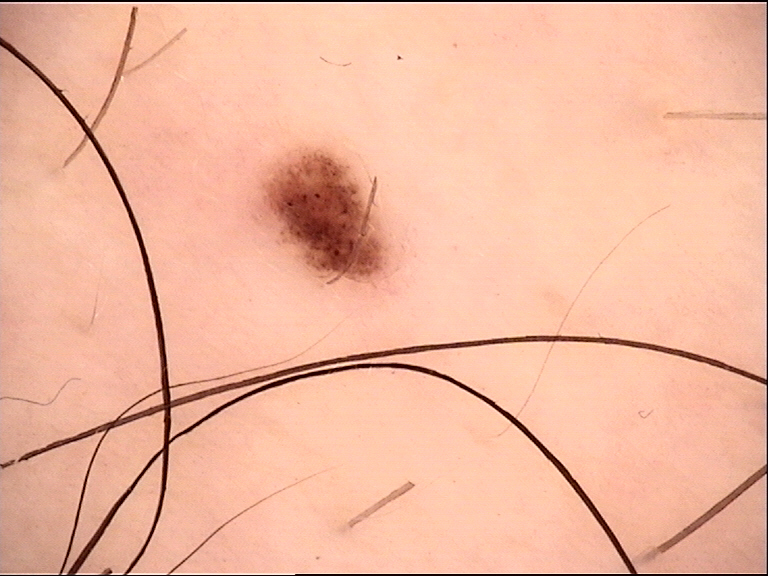class: dysplastic junctional nevus (expert consensus).